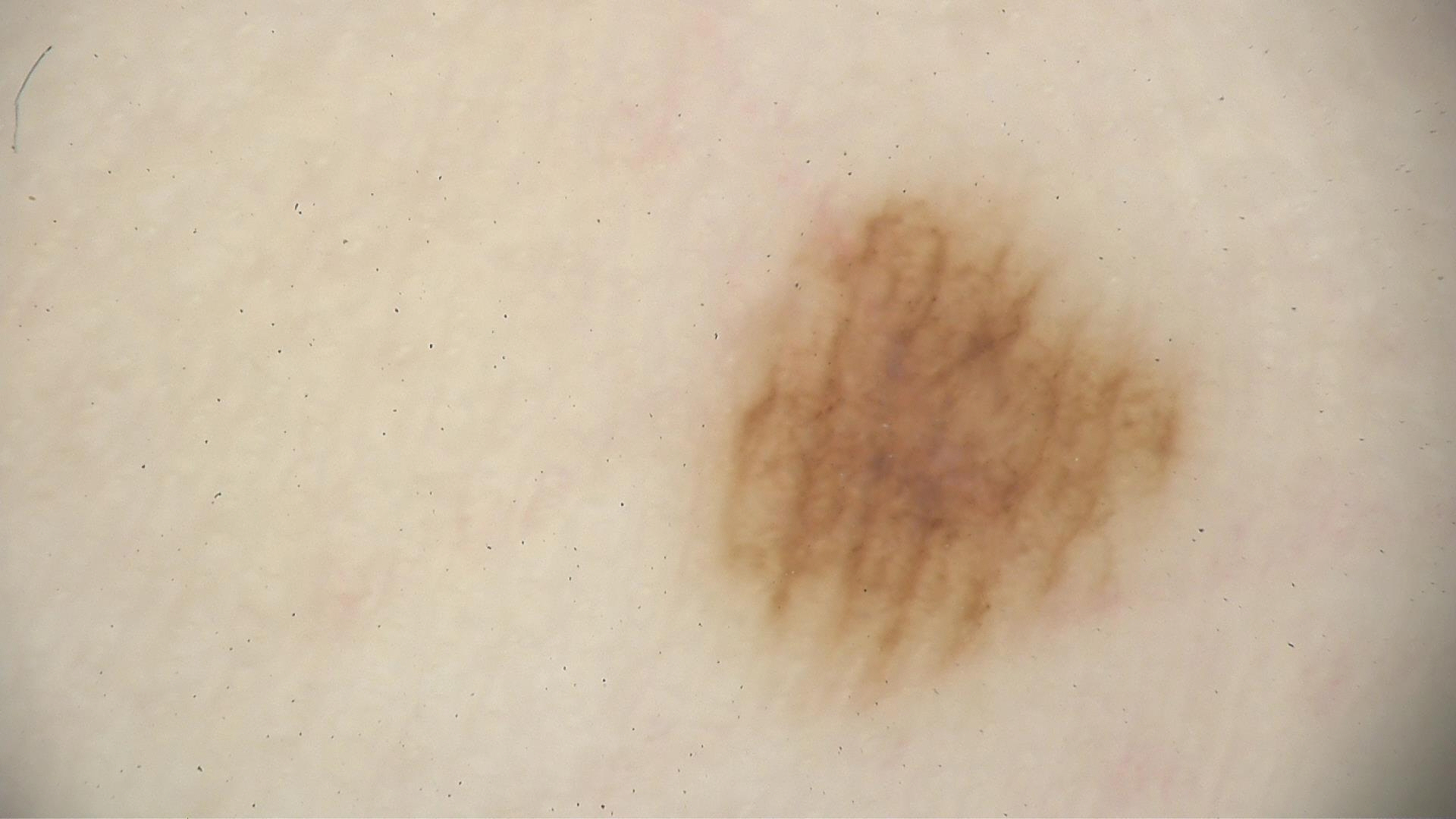| feature | finding |
|---|---|
| modality | dermoscopy |
| diagnosis | acral dysplastic junctional nevus (expert consensus) |